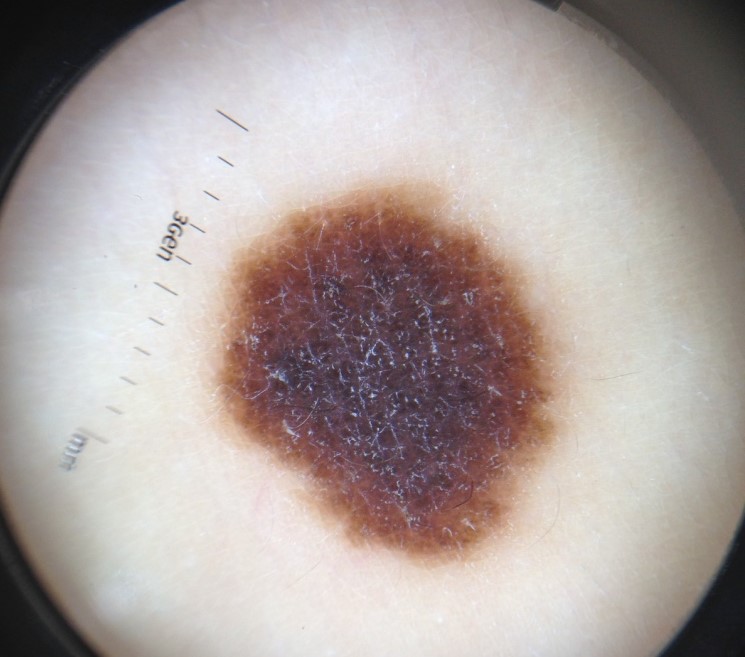Q: What is the diagnosis?
A: congenital compound nevus (expert consensus)